Dermoscopy of a skin lesion.
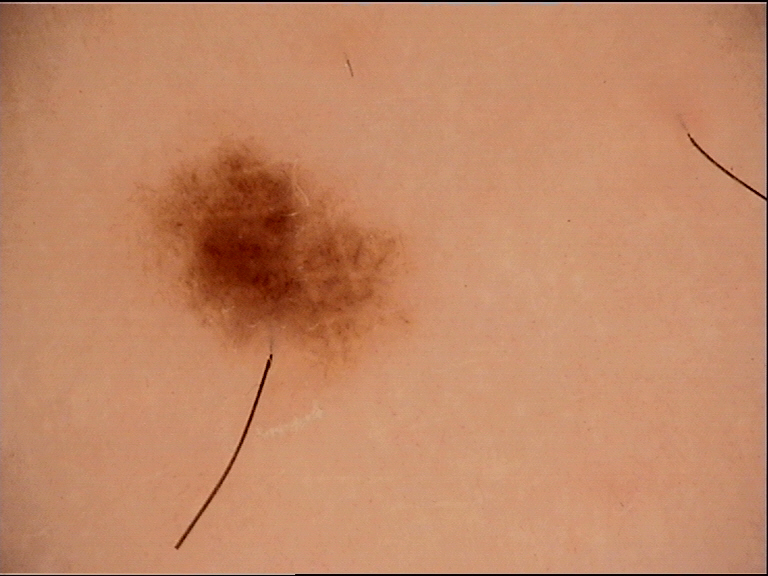The diagnosis was a dysplastic junctional nevus.